The lesion is described as raised or bumpy · the affected area is the front of the torso, back of the hand, leg and arm · the contributor reports itching · self-categorized by the patient as a rash · an image taken at a distance.
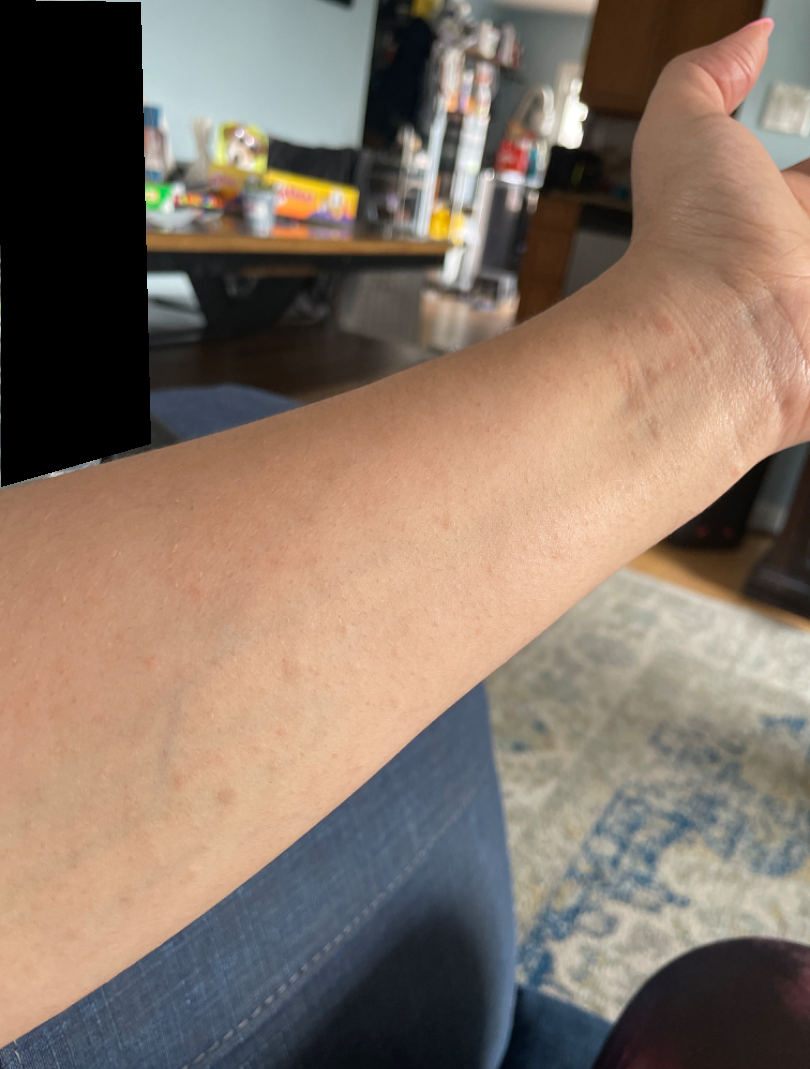assessment: indeterminate.